A dermoscopic image of a skin lesion: 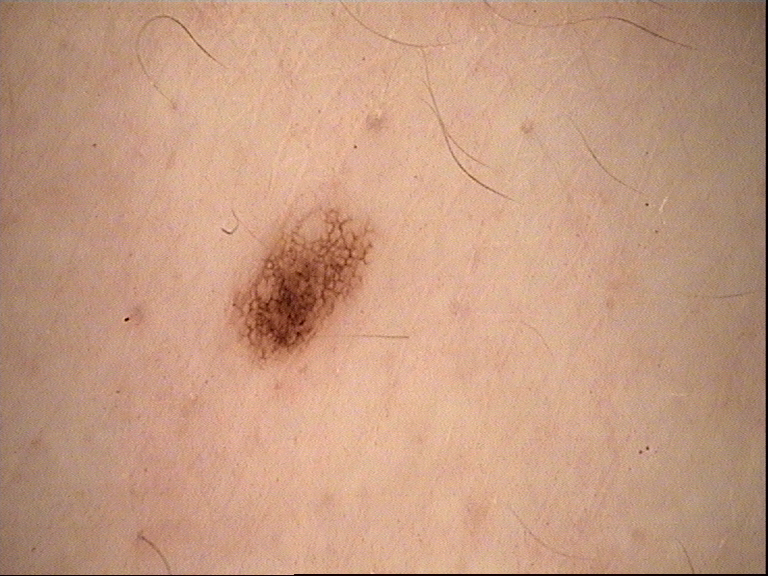Q: What is this lesion?
A: dysplastic junctional nevus (expert consensus)